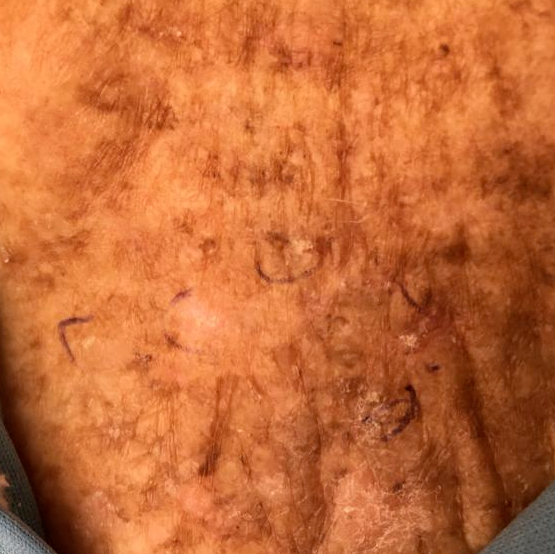{
  "image": "clinical photograph",
  "patient": {
    "age": 59,
    "gender": "female"
  },
  "symptoms": {
    "present": [
      "itching"
    ],
    "absent": [
      "growth"
    ]
  },
  "diagnosis": {
    "name": "actinic keratosis",
    "code": "ACK",
    "malignancy": "indeterminate",
    "confirmation": "clinical consensus"
  }
}